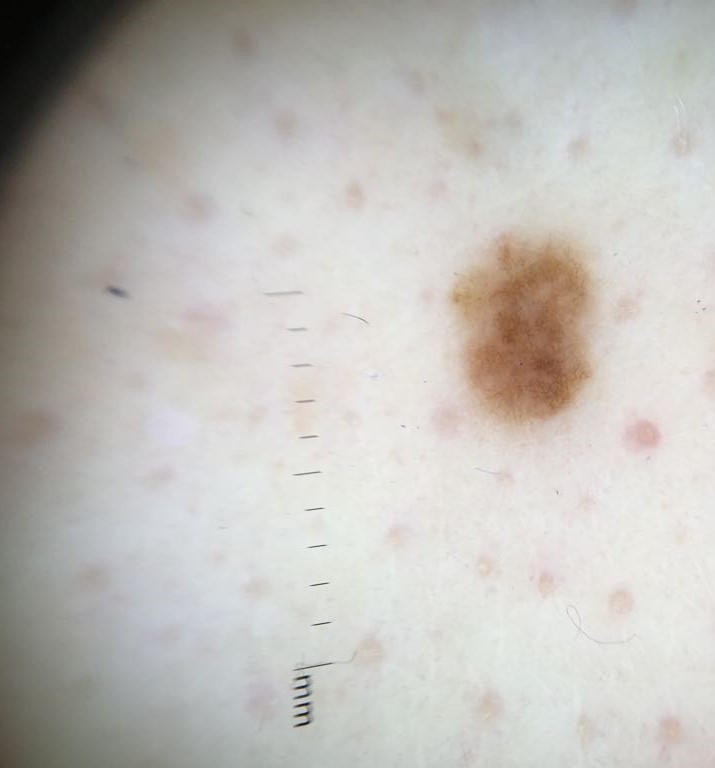Q: What is this lesion?
A: dysplastic junctional nevus (expert consensus)